A close-up photograph; located on the arm; the patient described the issue as a growth or mole; the patient is male; the patient indicates the condition has been present for three to twelve months.
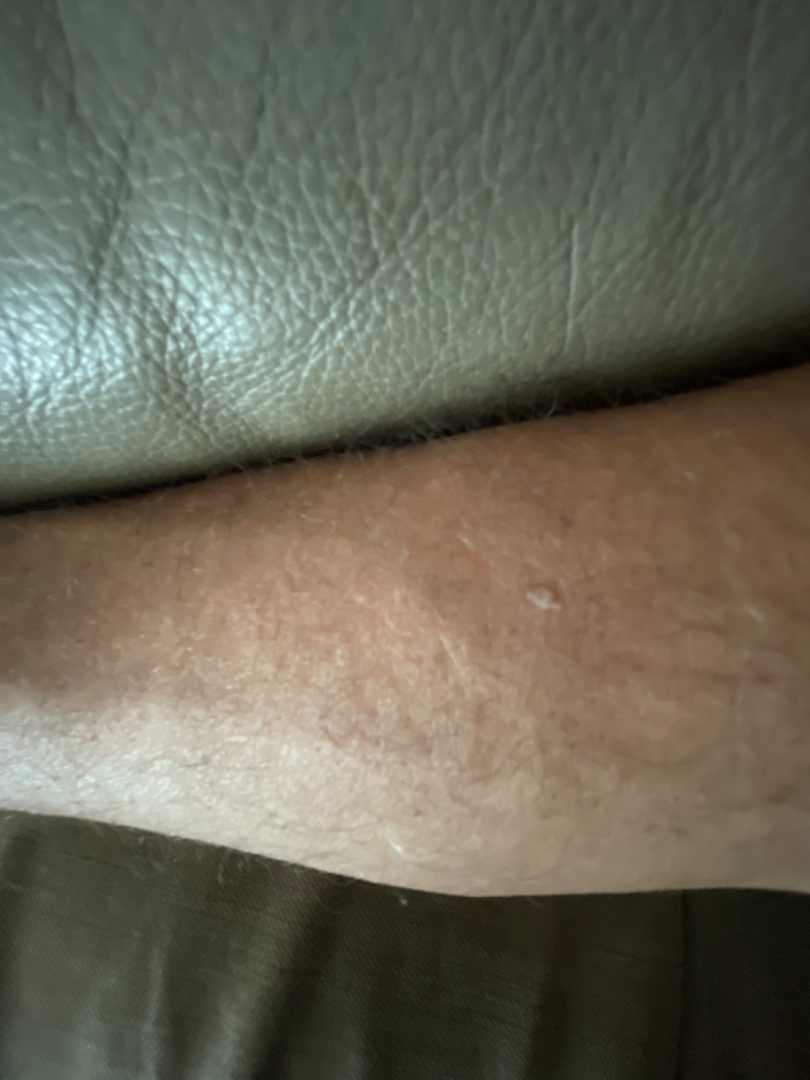Assessment:
The dermatologist could not determine a likely condition from the photograph alone.